A dermoscopic image of a skin lesion, the patient is a female aged 28 to 32:
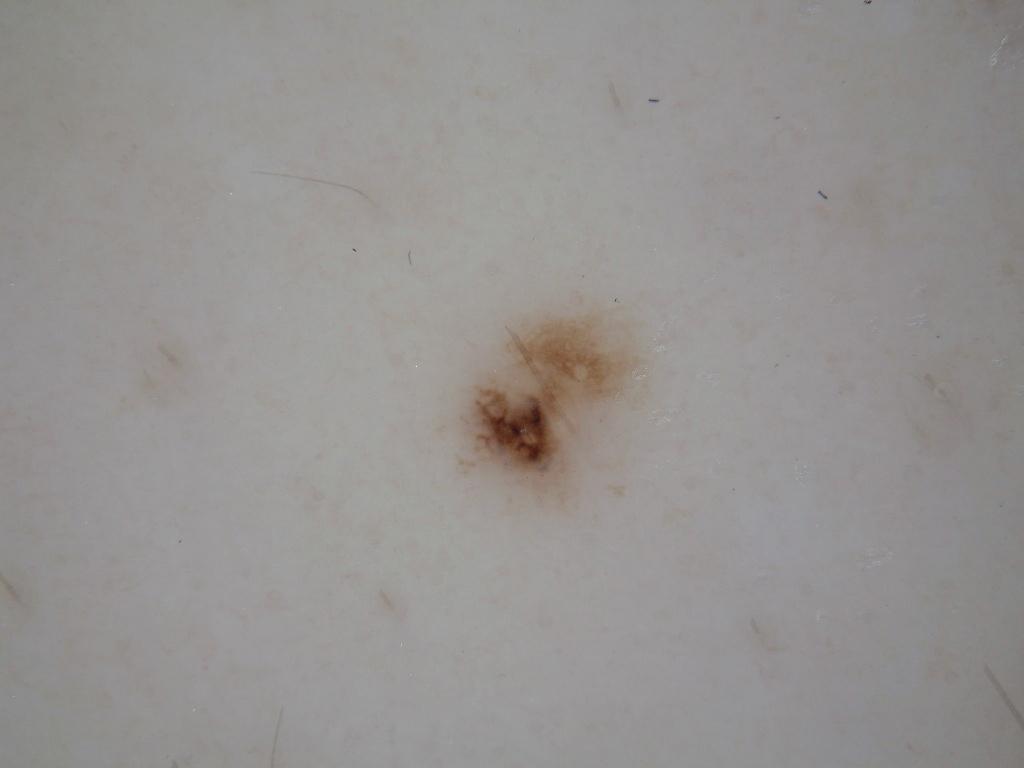dermoscopic_features:
  present:
    - pigment network
  absent:
    - milia-like cysts
    - globules
    - streaks
    - negative network
lesion_location:
  bbox_xyxy:
    - 458
    - 307
    - 639
    - 502
lesion_extent:
  approx_field_fraction_pct: 3
diagnosis:
  name: melanocytic nevus
  malignancy: benign
  lineage: melanocytic
  provenance: clinical